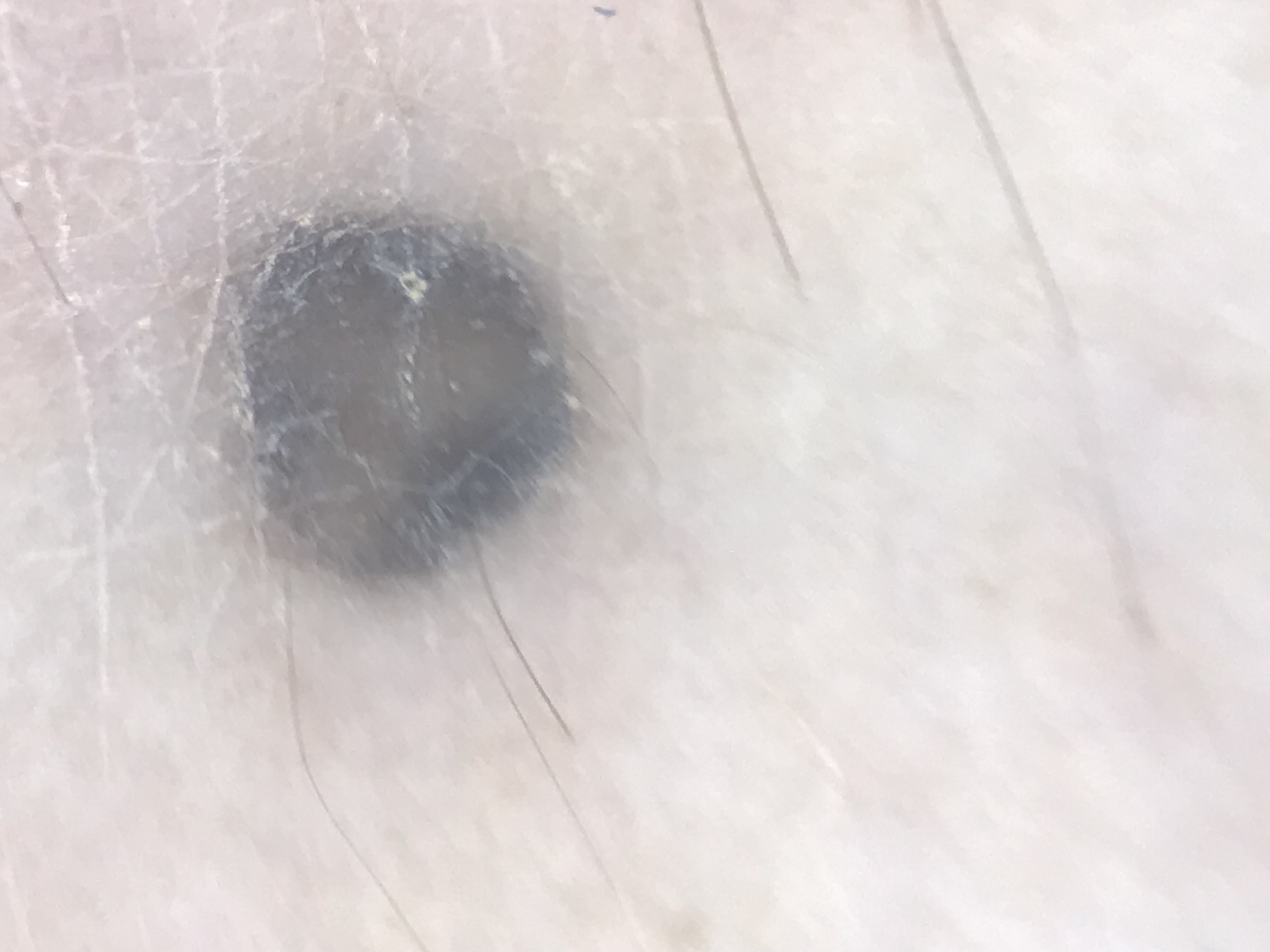  image: dermoscopy
  lesion_type:
    main_class: banal
    pattern: dermal
  diagnosis:
    name: blue nevus
    code: bdb
    malignancy: benign
    super_class: melanocytic
    confirmation: expert consensus